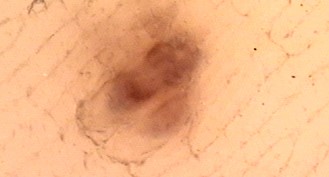A dermoscopy image of a single skin lesion.
The architecture is that of a banal lesion.
Classified as an acral compound nevus.